A dermoscopy image of a single skin lesion:
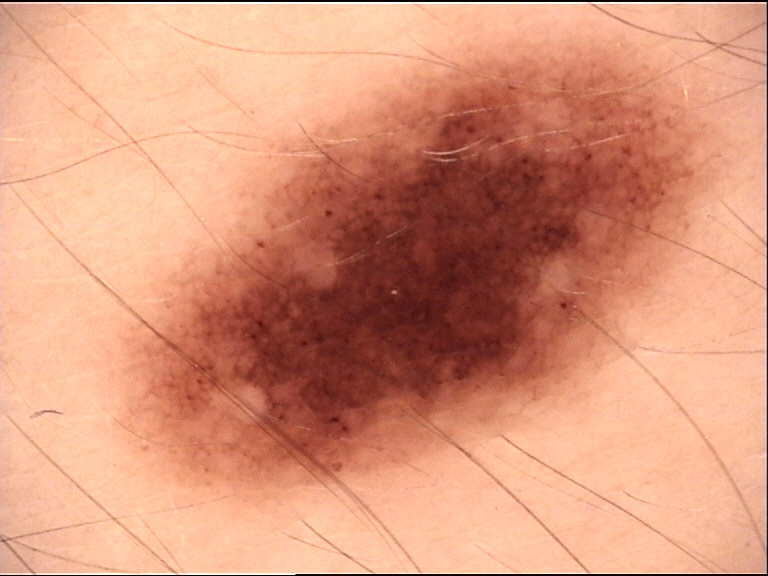Diagnosed as a benign lesion — a dysplastic junctional nevus.